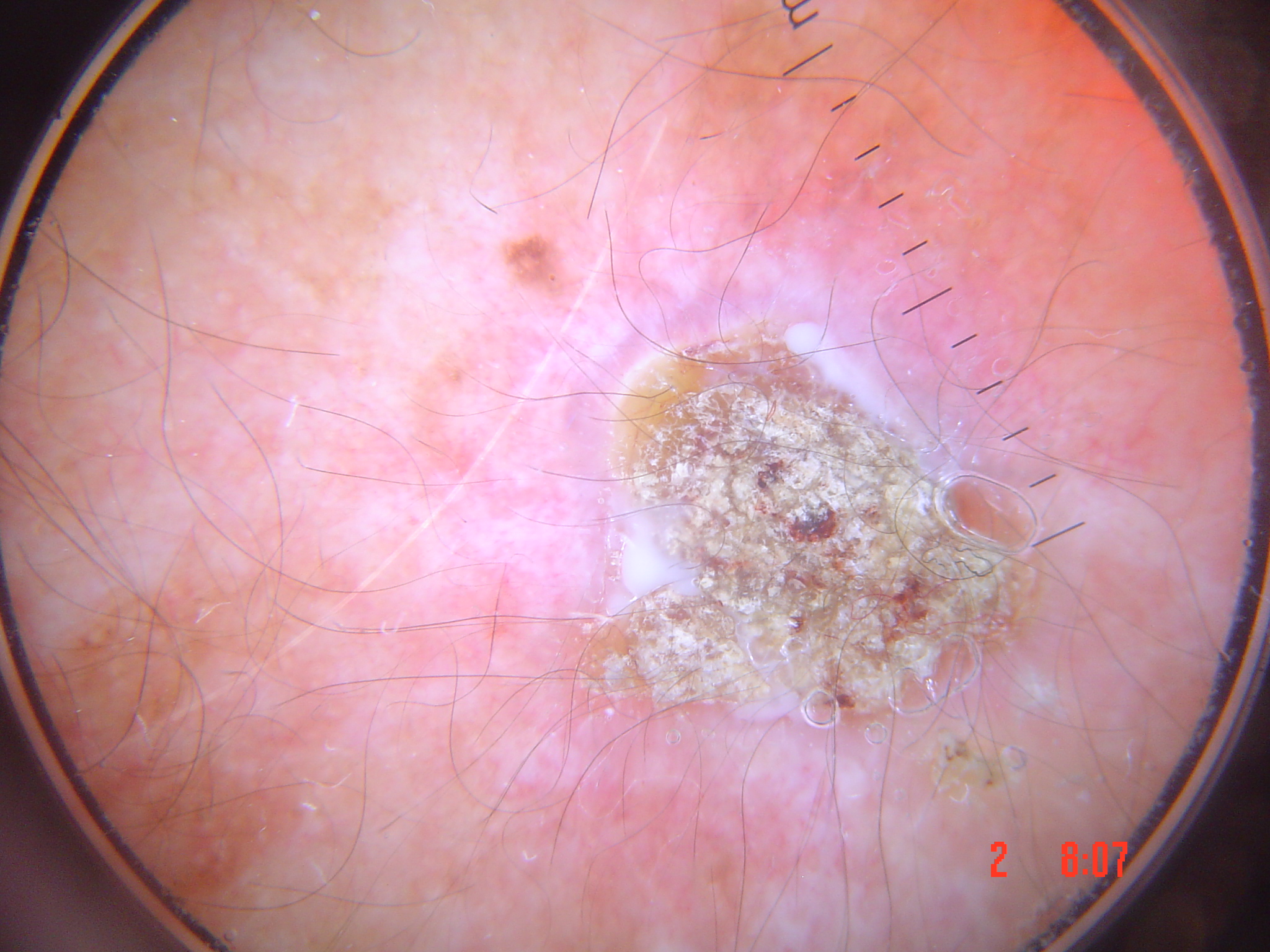The biopsy diagnosis was a squamous cell carcinoma.